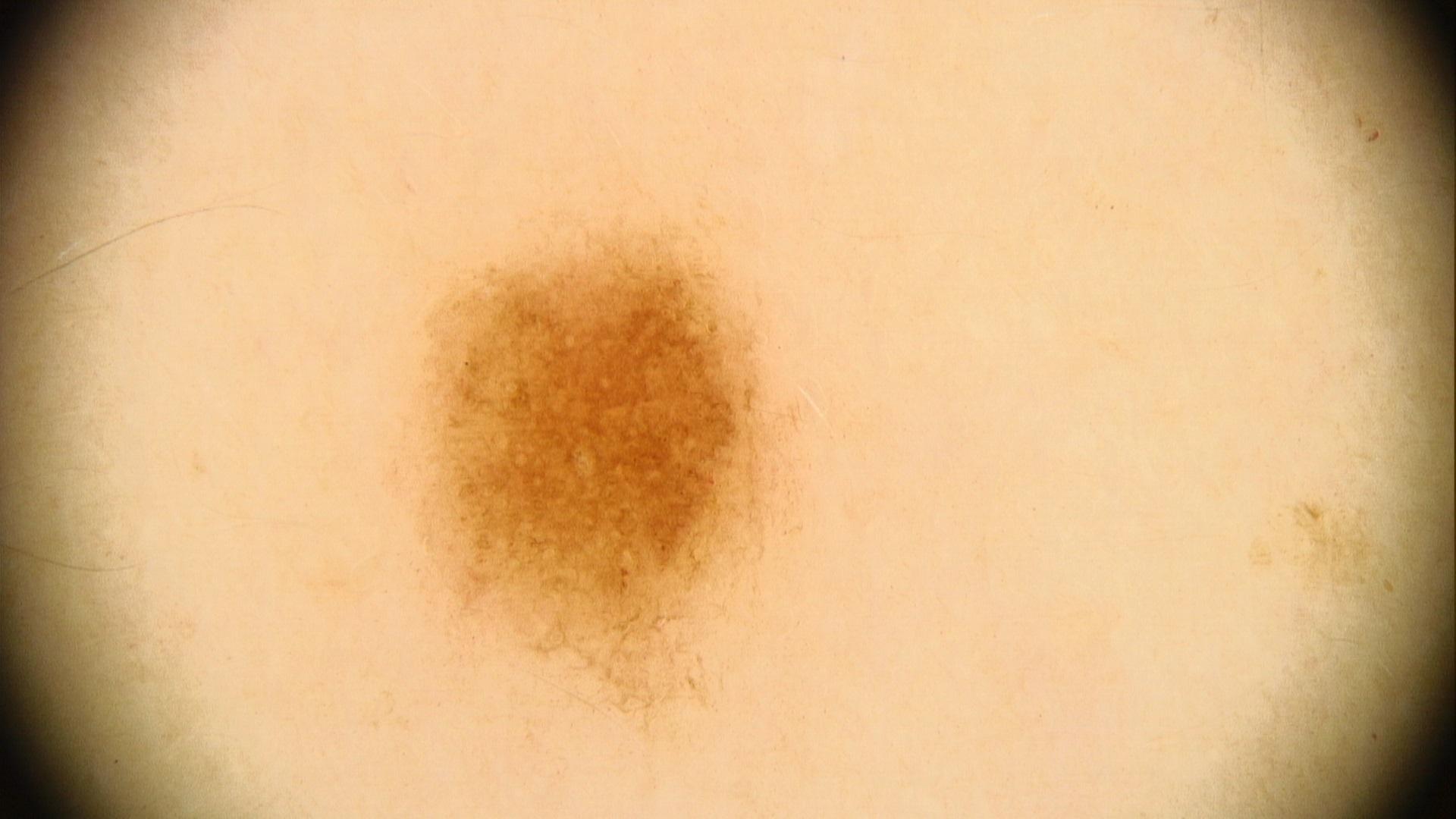Image and clinical context:
A male patient about 40 years old. Per the chart, melanoma in a first-degree relative but no previous melanoma.
Assessment:
Consistent with a nevus.